A skin lesion imaged with a dermatoscope; the chart notes a previous melanoma; a male patient aged 83 or over; Fitzpatrick phototype II.
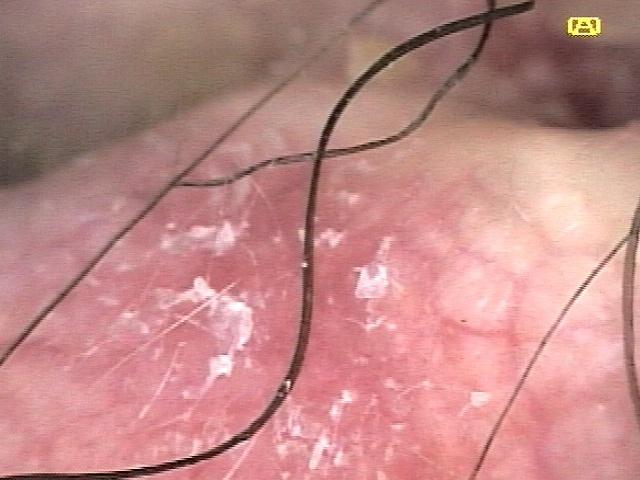diagnostic label = Solar or actinic keratosis (clinical impression).